A dermatoscopic image of a skin lesion · a female subject, aged around 75:
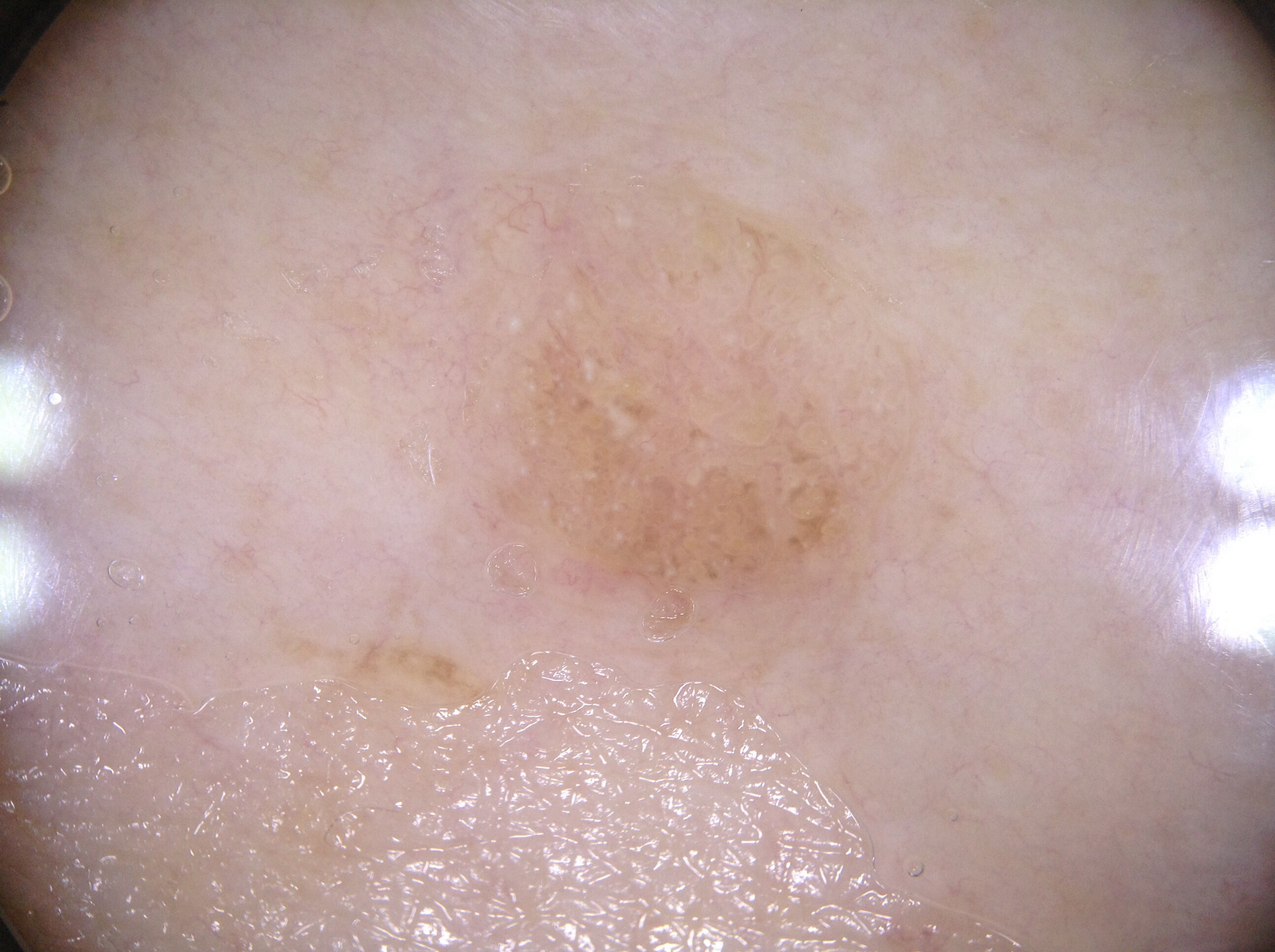As (left, top, right, bottom), the lesion is located at bbox=[464, 156, 919, 735].
On dermoscopy, the lesion shows milia-like cysts; no streaks, negative network, or pigment network.
The lesion was assessed as a seborrheic keratosis.